Recorded as Fitzpatrick phototype II. A skin lesion imaged with contact-polarized dermoscopy. A female subject aged around 70 — 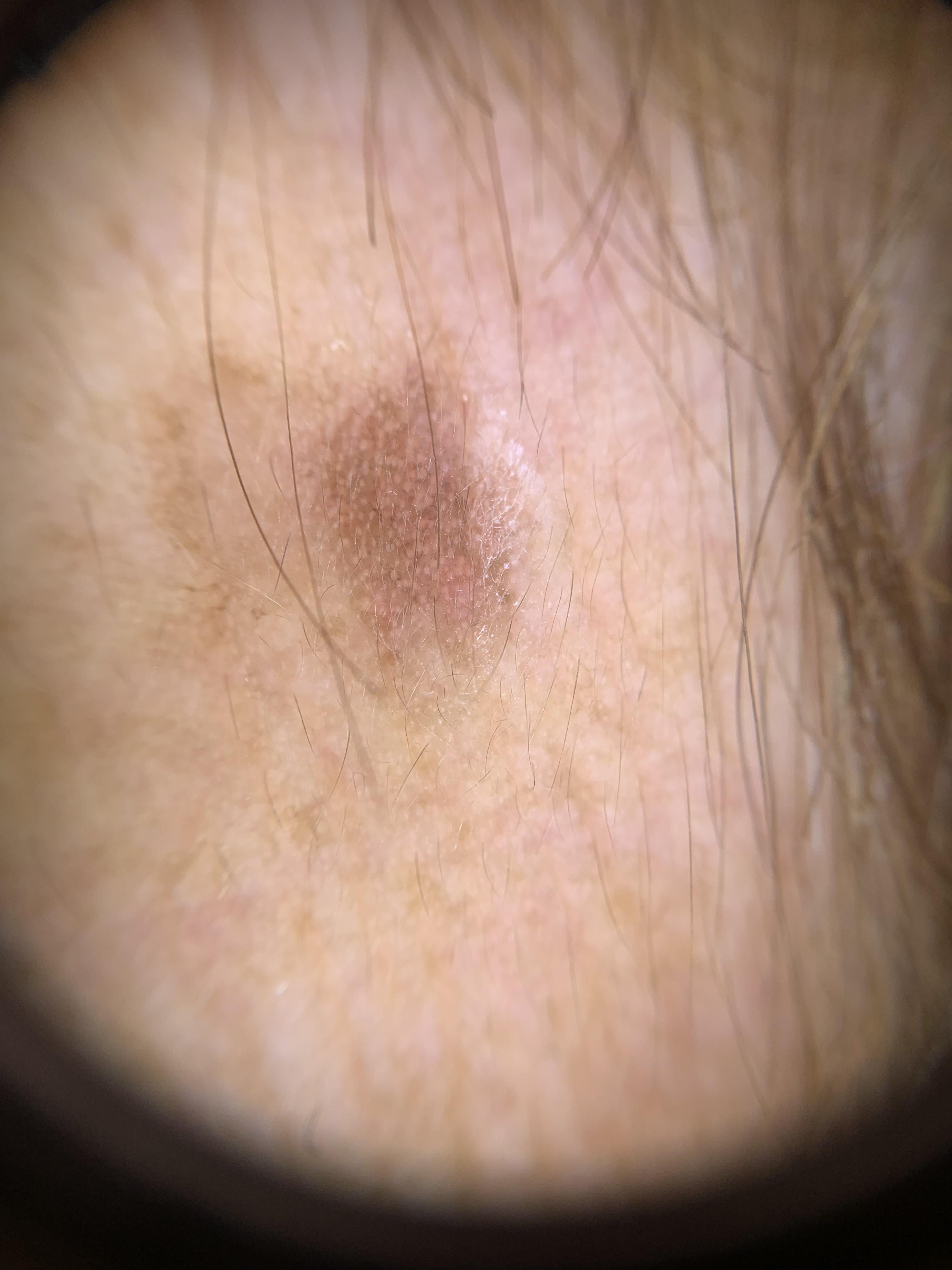Findings: The lesion is located on the head or neck. Impression: Clinically diagnosed as a premalignant, epidermal lesion — a solar or actinic keratosis.